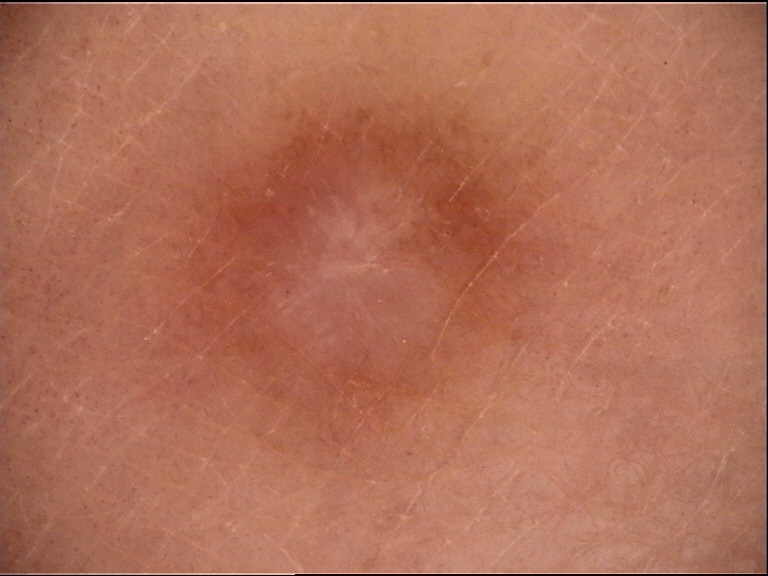A dermatoscopic image of a skin lesion.
Labeled as a benign lesion — a dermatofibroma.